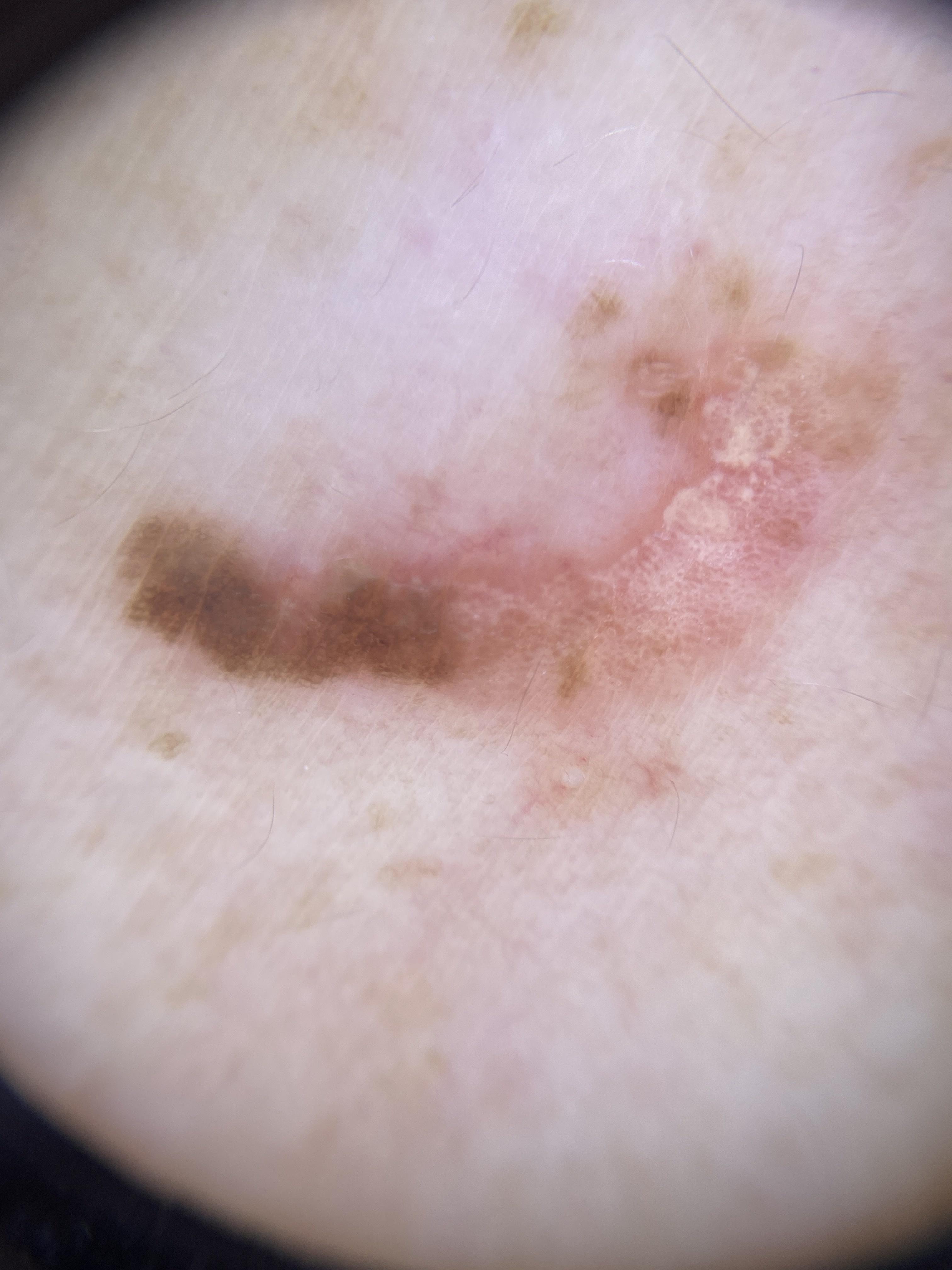Per the chart, no previous melanoma and no first-degree relative with melanoma.
A skin lesion imaged with contact-polarized dermoscopy.
The lesion is located on the trunk, specifically the posterior trunk.
The biopsy diagnosis was a malignant lesion — a melanoma.